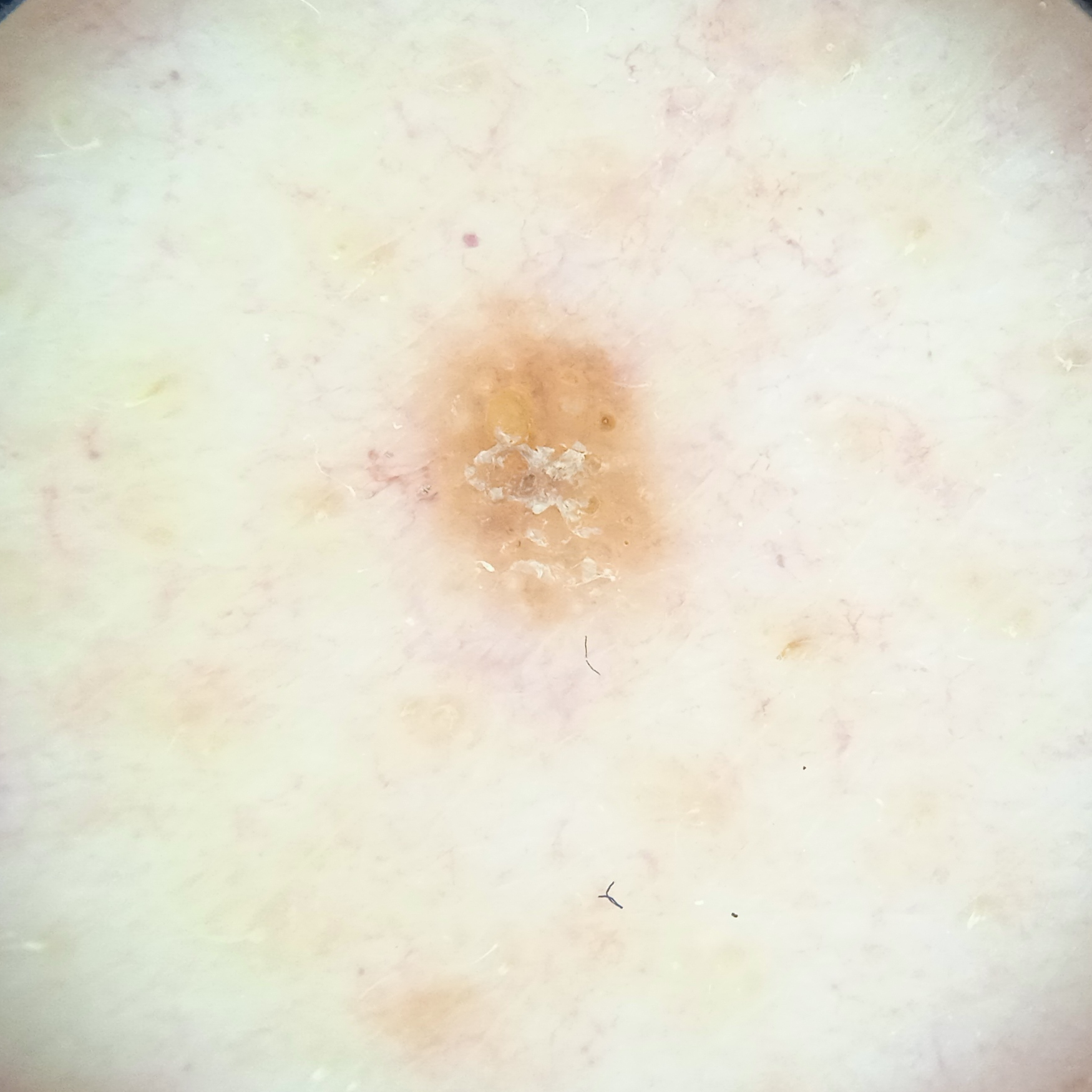{
  "sun_reaction": "skin reddens painfully with sun exposure",
  "mole_burden": "numerous melanocytic nevi",
  "referral": "research study (no referral diagnosis)",
  "risk_factors": {
    "positive": [
      "immunosuppression",
      "a personal history of skin cancer",
      "a family history of skin cancer"
    ]
  },
  "patient": {
    "age": 65,
    "sex": "male"
  },
  "image": "dermatoscopic image",
  "lesion_location": "the back",
  "lesion_size": {
    "diameter_mm": 3.3
  },
  "diagnosis": {
    "name": "seborrheic keratosis",
    "malignancy": "benign"
  }
}